This is a close-up image · located on the back of the torso · the patient is a female aged 18–29: 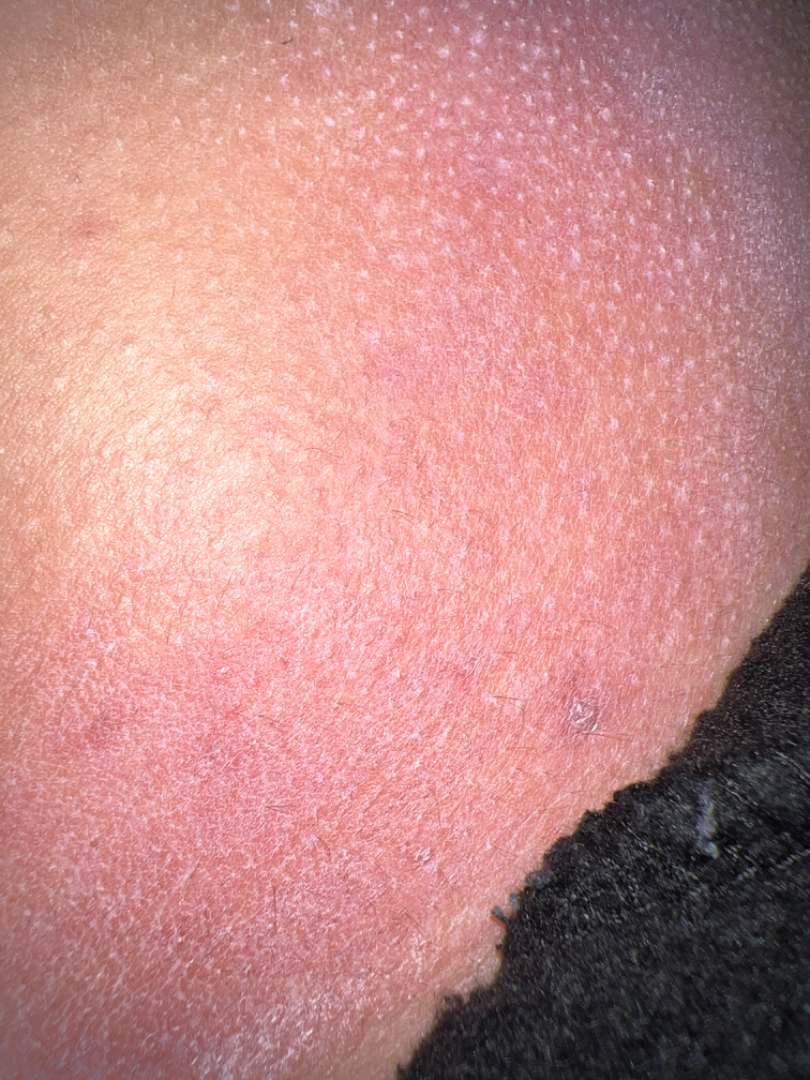assessment: ungradable on photographic review.